Close-up view — 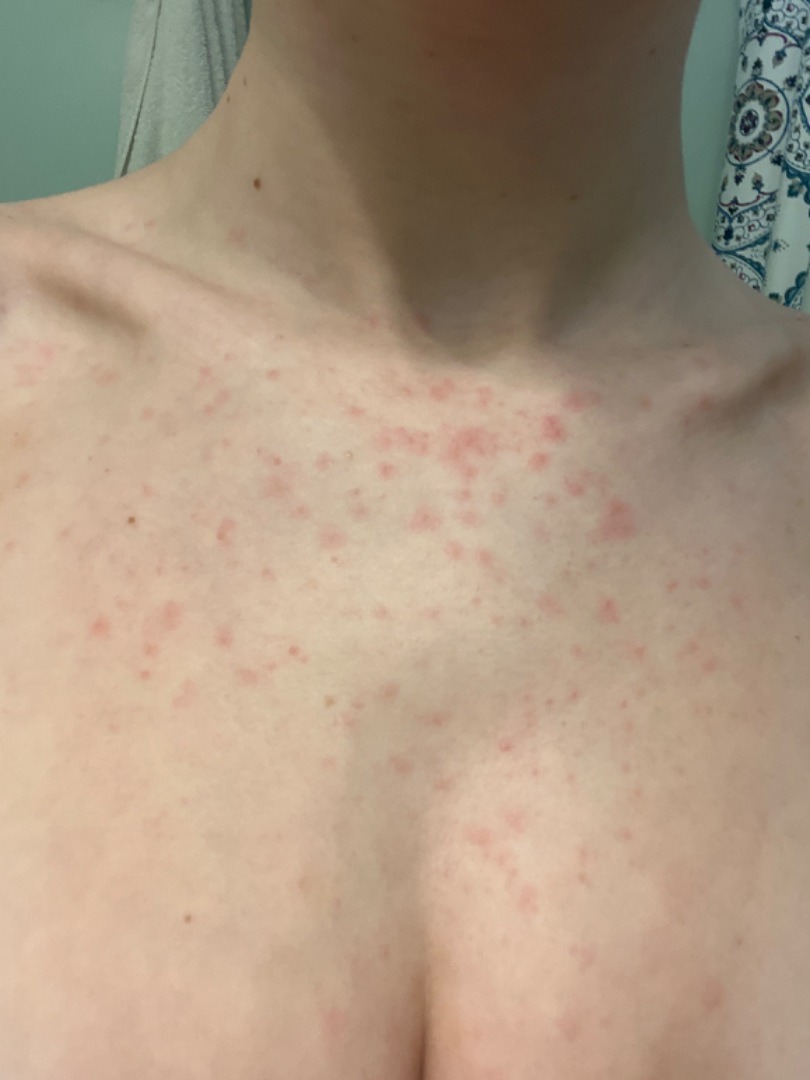{"patient_category": "a rash", "texture": "raised or bumpy", "systemic_symptoms": "none reported", "duration": "about one day", "symptoms": "none reported", "differential": {"leading": ["telangiectasia macularis eruptiva perstans"], "considered": ["Folliculitis", "Acute dermatitis, NOS"]}}